This is a close-up image. Skin tone: lay graders estimated Monk skin tone scale 6 (US pool) or 4 (India pool): 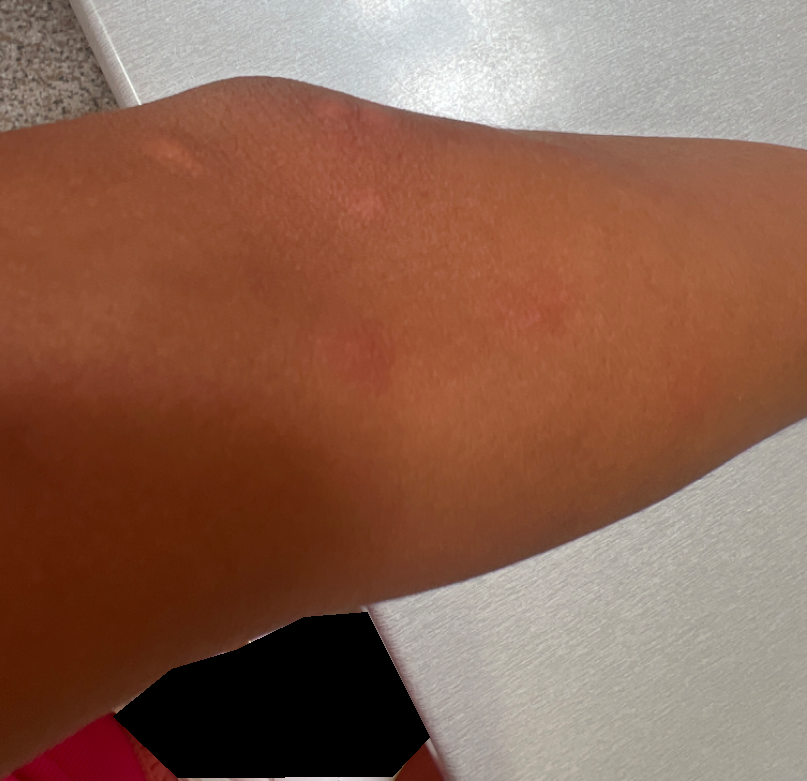assessment=unable to determine.